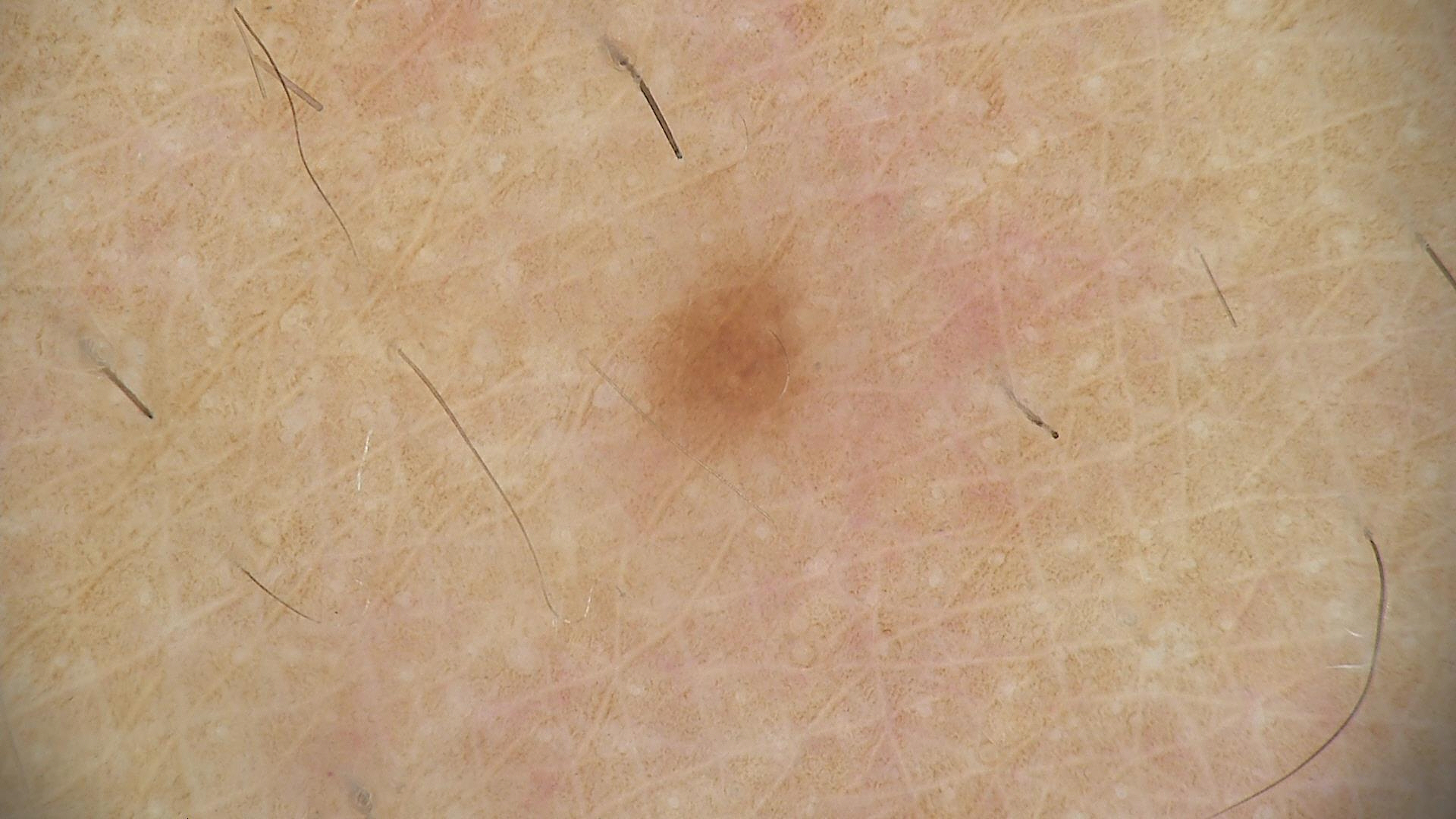Impression: Consistent with a dysplastic junctional nevus.